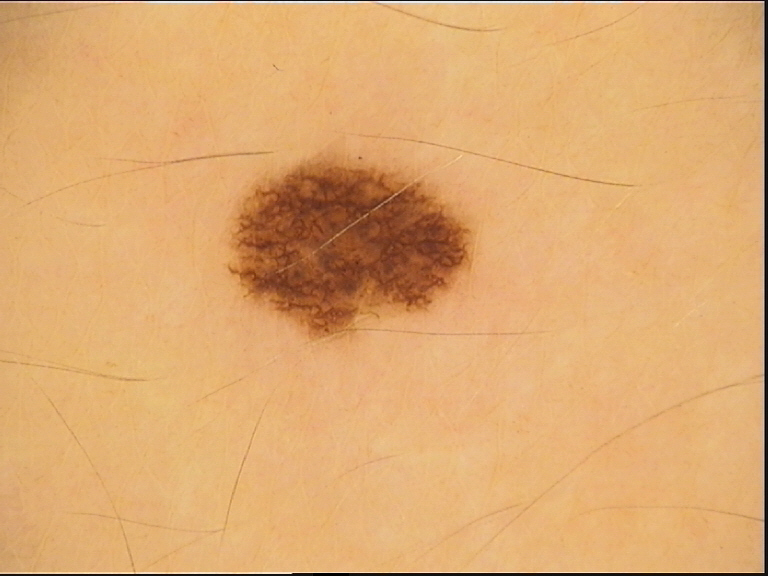Conclusion:
The diagnostic label was a dysplastic junctional nevus.